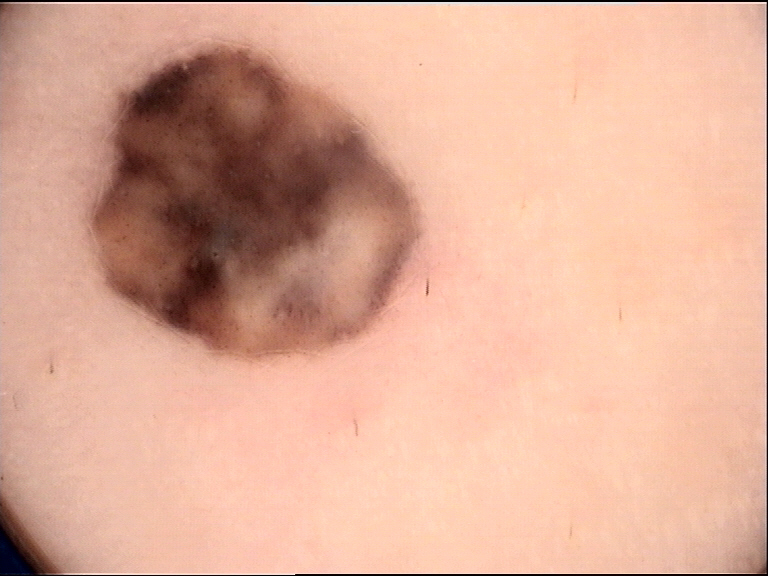image = dermoscopy, diagnosis = blue nevus (expert consensus).